Texture is reported as rough or flaky, this is a close-up image, located on the head or neck — 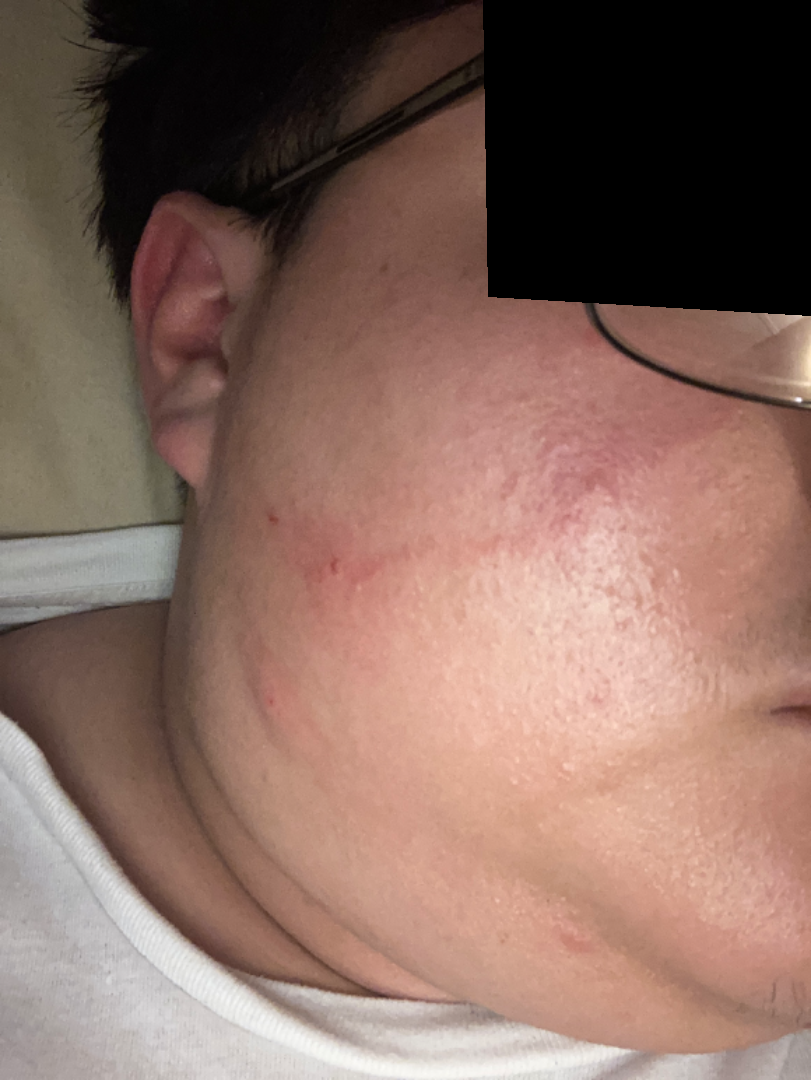{
  "differential": {
    "leading": [
      "Acne"
    ],
    "considered": [
      "Irritant Contact Dermatitis"
    ]
  }
}